A female patient aged approximately 65.
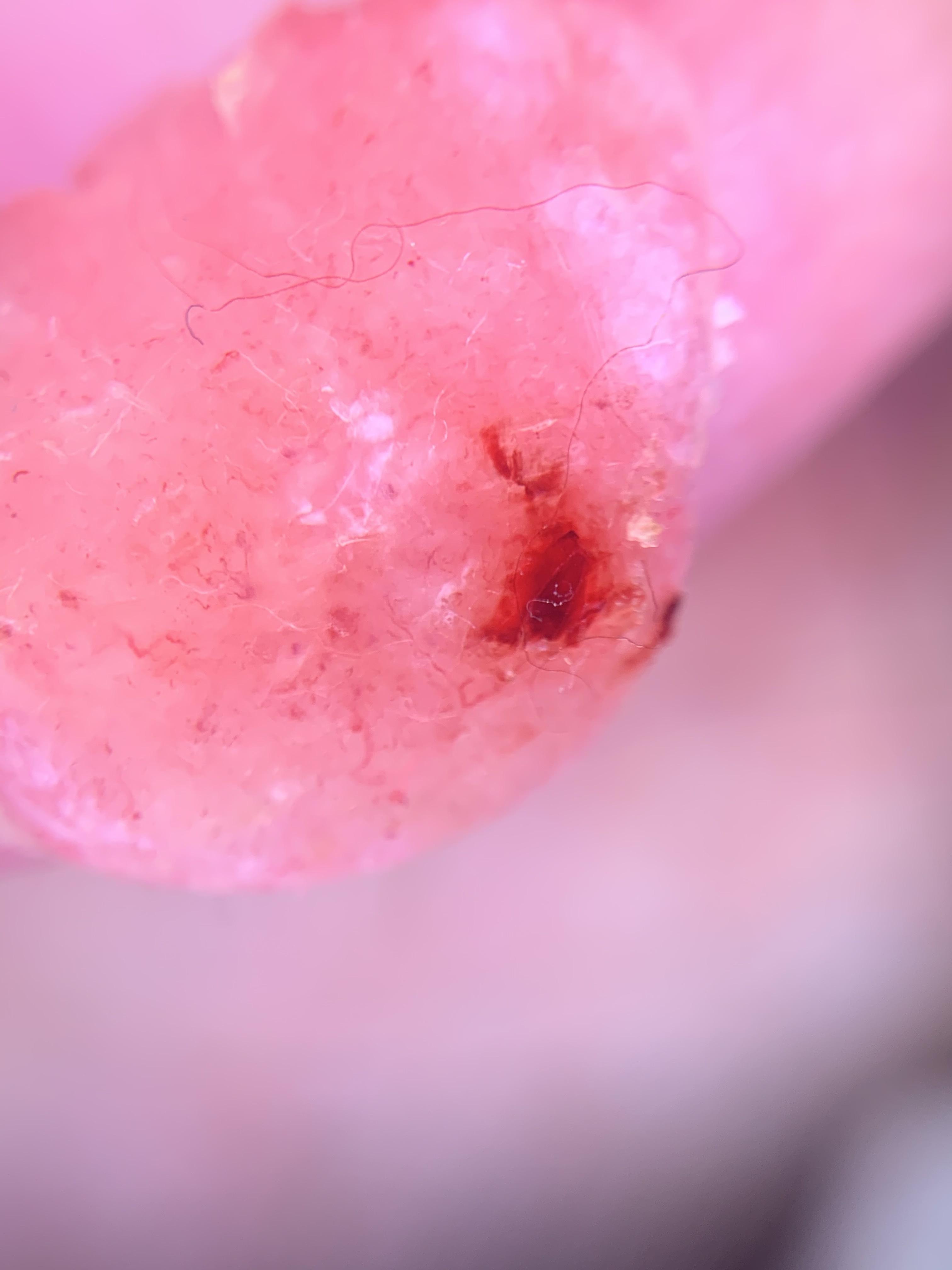<case>
<diagnosis>
<name>Squamous cell carcinoma</name>
<malignancy>malignant</malignancy>
<confirmation>histopathology</confirmation>
<lineage>epidermal</lineage>
</diagnosis>
</case>